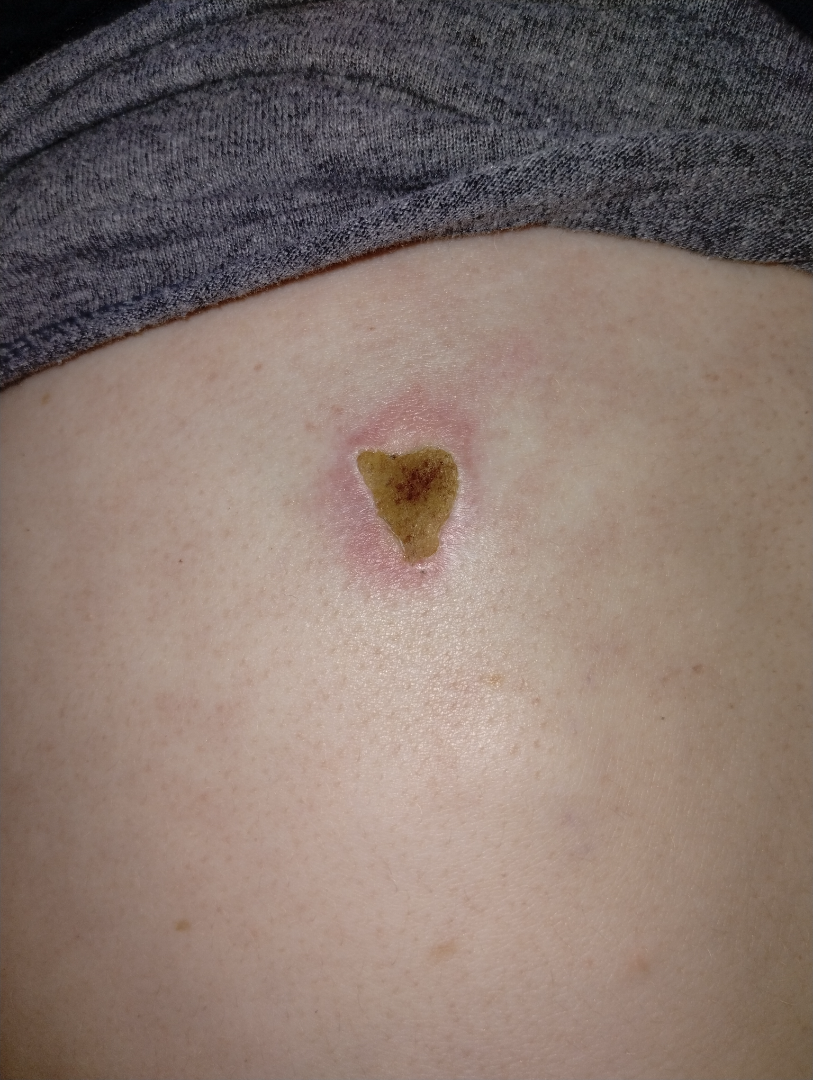The skin findings could not be characterized from the image.